The photograph is a close-up of the affected area:
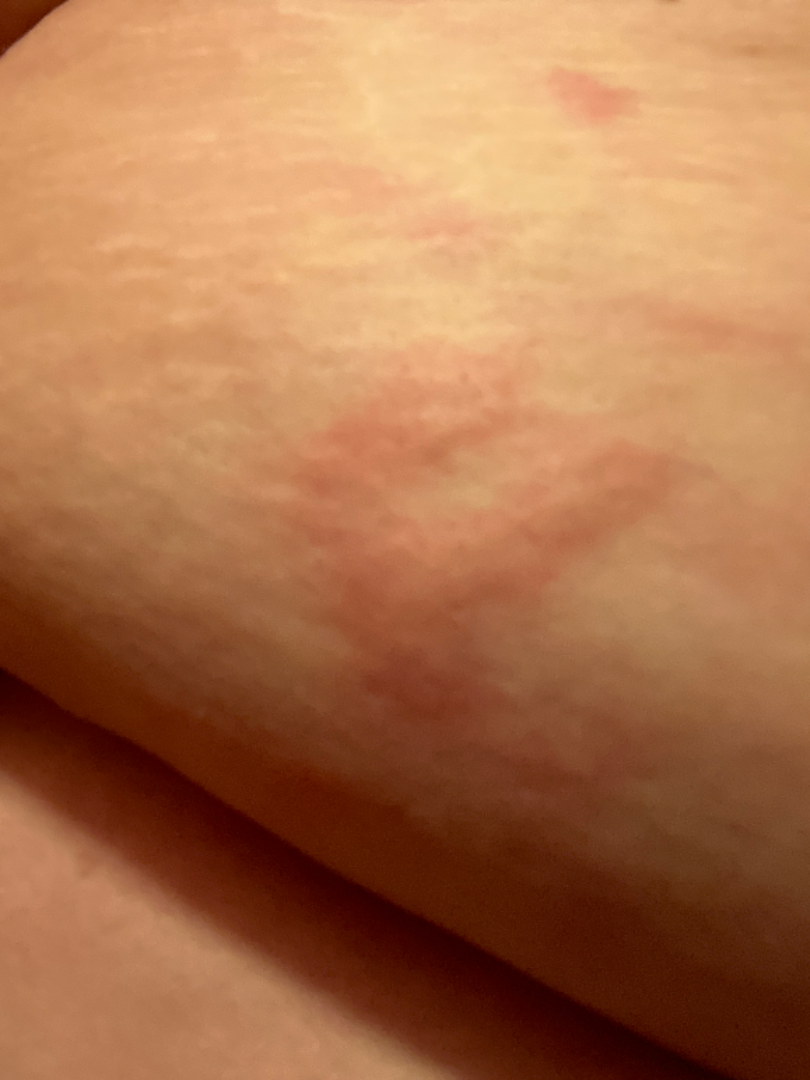Findings: Diagnostic features were not clearly distinguishable in this photograph.